A dermoscopic view of a skin lesion · a female subject aged approximately 80: 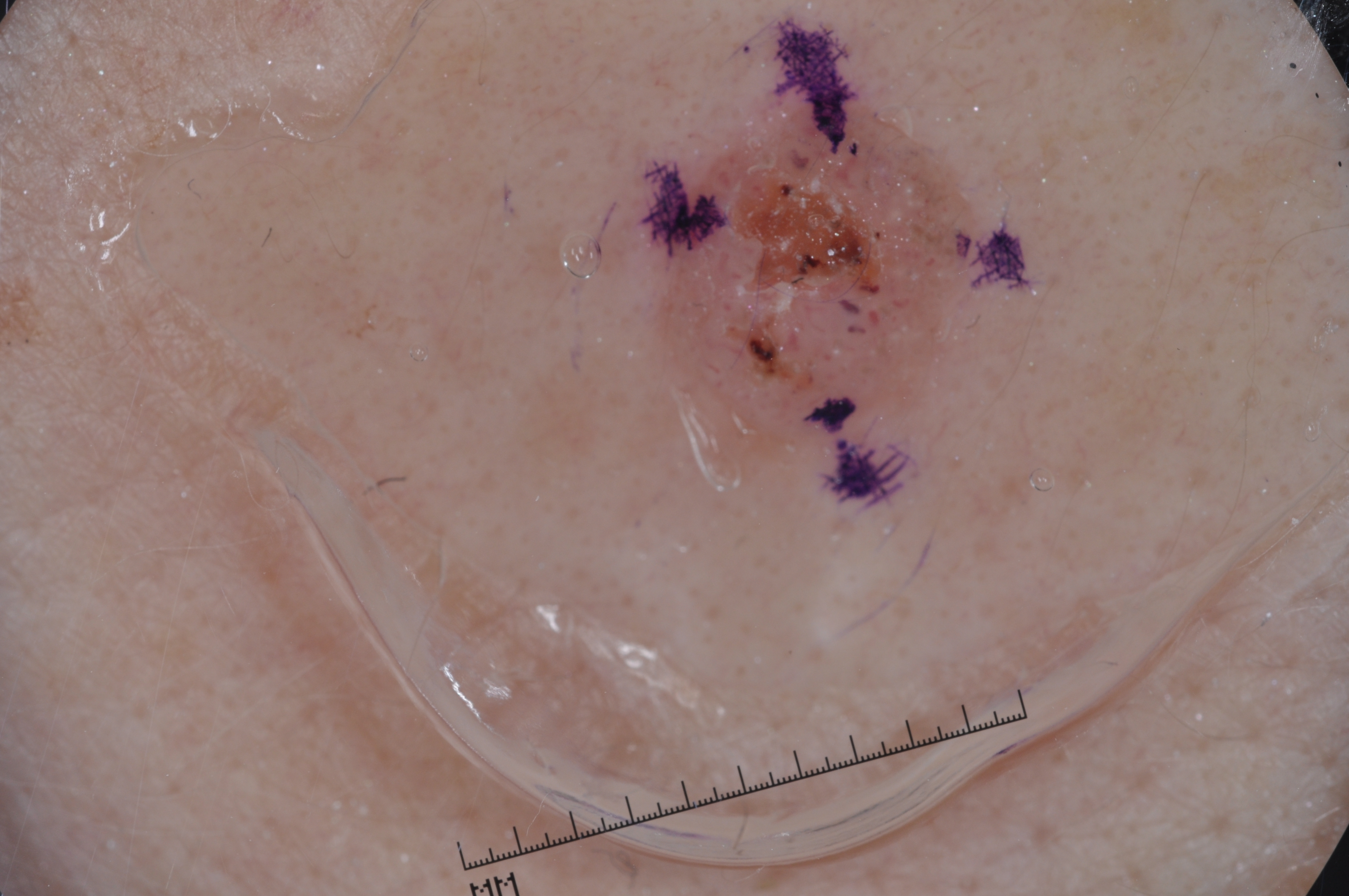<record>
<dermoscopic_features>
  <present>milia-like cysts</present>
  <absent>negative network, pigment network, streaks</absent>
</dermoscopic_features>
<lesion_location>
  <bbox_xyxy>639, 59, 1005, 460</bbox_xyxy>
</lesion_location>
<lesion_extent>moderate</lesion_extent>
<diagnosis>
  <name>seborrheic keratosis</name>
  <malignancy>benign</malignancy>
  <lineage>keratinocytic</lineage>
  <provenance>clinical</provenance>
</diagnosis>
</record>